The subject is a female aged 50–59. The arm and back of the hand are involved. The patient notes the condition has been present for less than one week. The patient notes the lesion is flat. A close-up photograph.
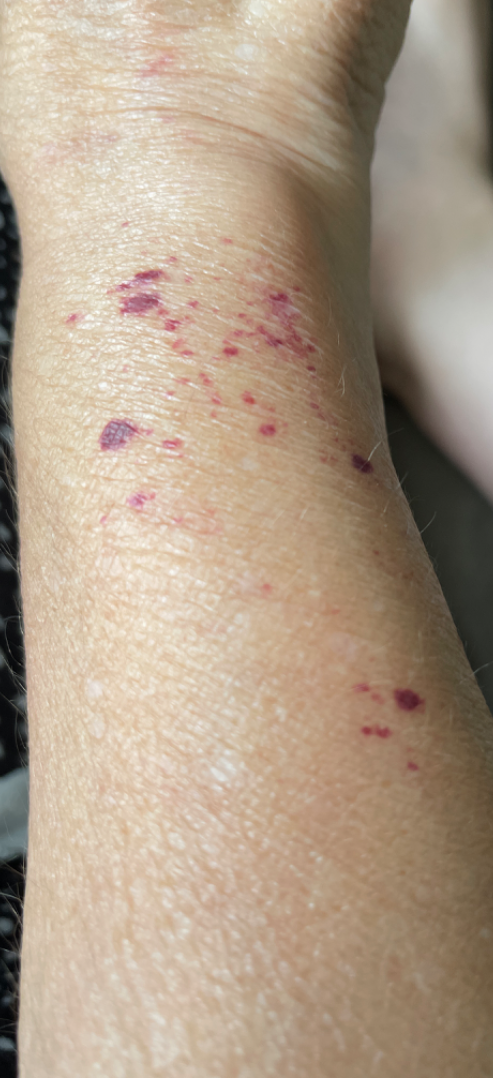differential diagnosis = the impression is ecchymoses.